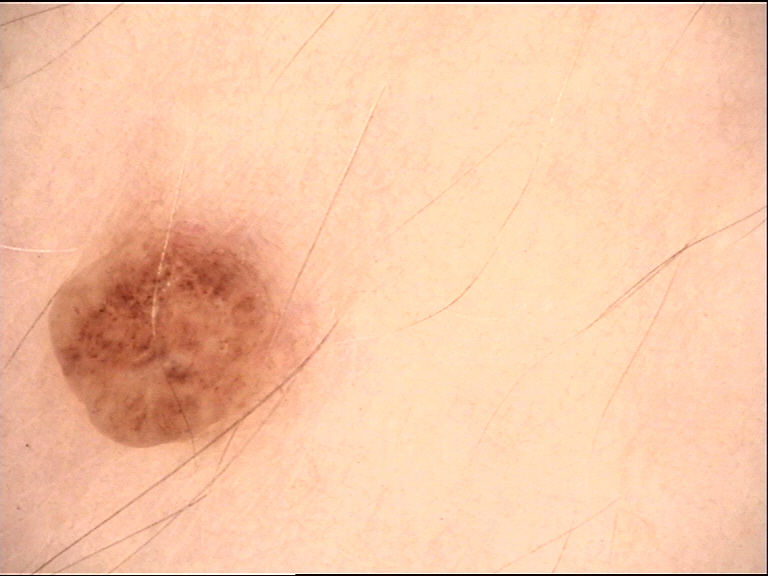label=dermal nevus (expert consensus)